A male subject in their mid-70s · a clinical photograph showing a skin lesion in context.
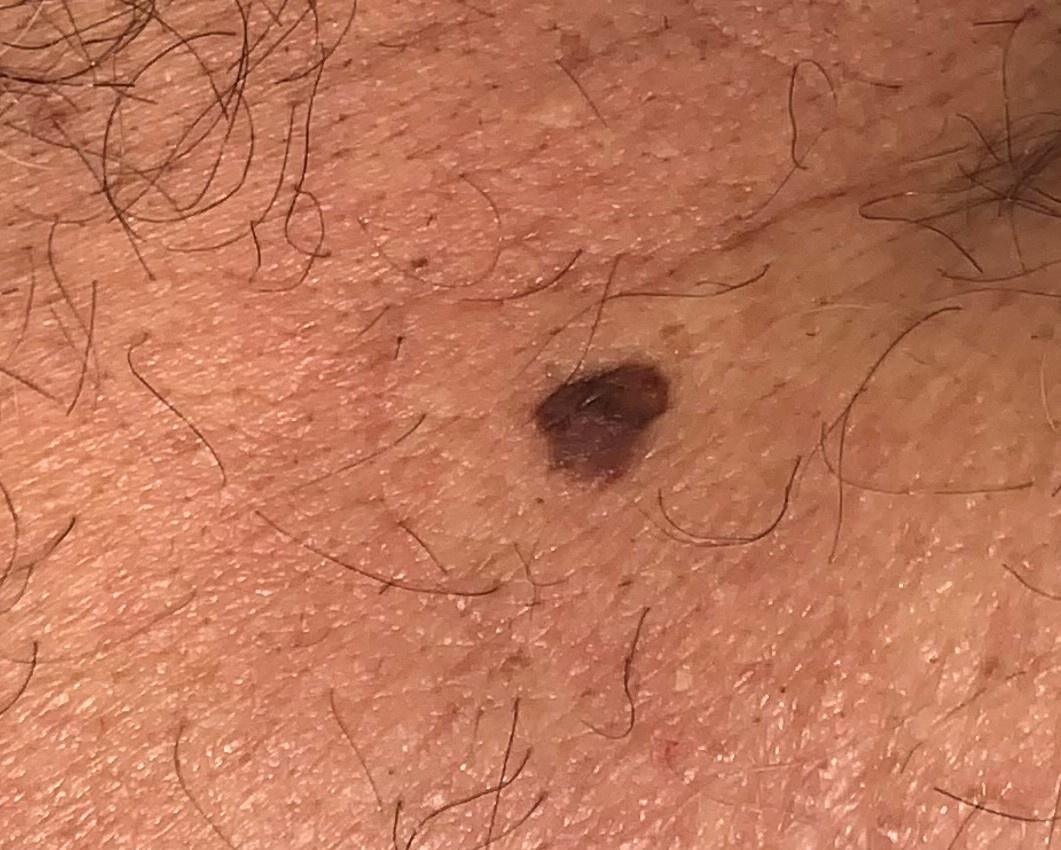| feature | finding |
|---|---|
| location | the head or neck |
| diagnostic label | Nevus (biopsy-proven) |